Recorded as Fitzpatrick phototype III — 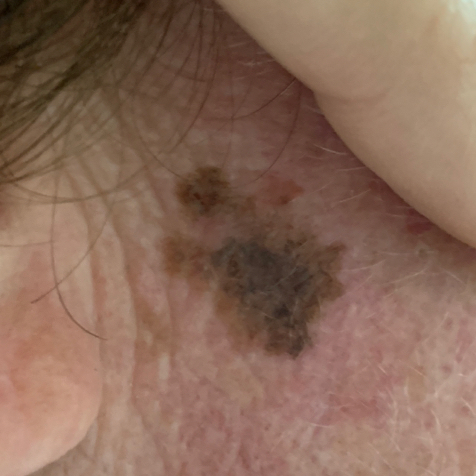Patient and lesion: The lesion involves the face. The lesion is roughly 12 by 5 mm. The patient reports that the lesion has grown, has changed, and itches. Conclusion: Confirmed on histopathology as a melanoma.